Skin tone: Fitzpatrick skin type II; a close-up photograph — 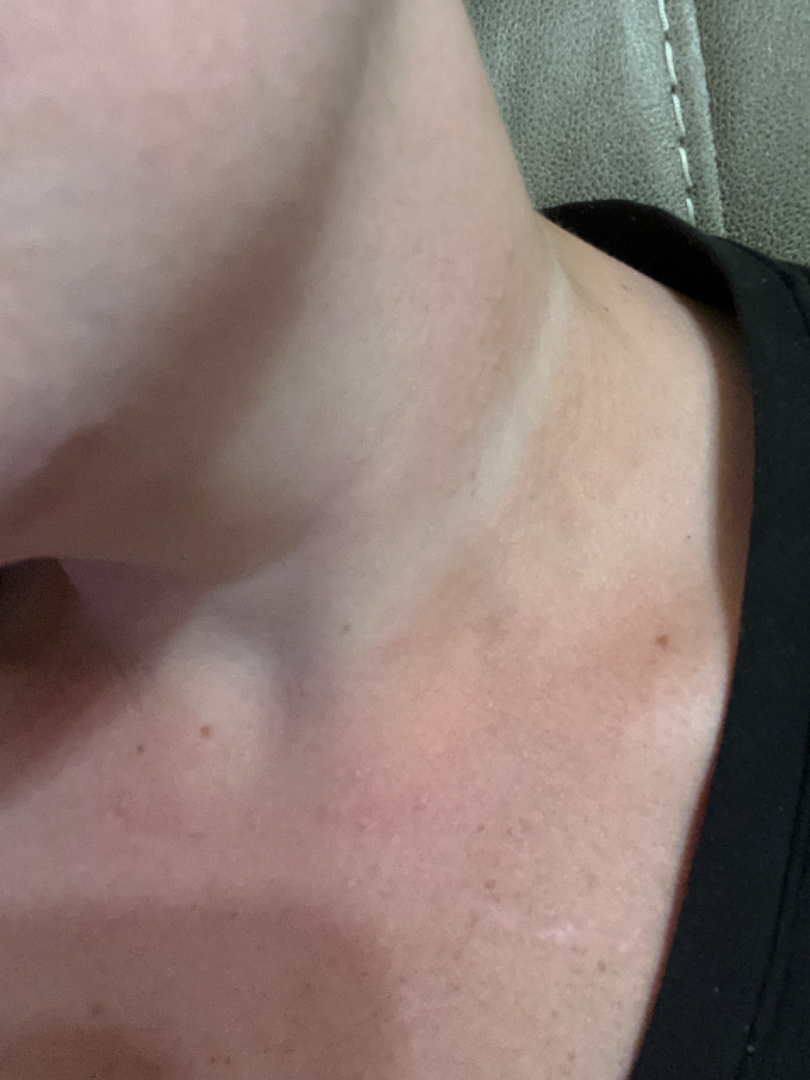No clear dermatological pathology was apparent in the photograph.